A dermoscopy image of a single skin lesion; a male patient, approximately 45 years of age: 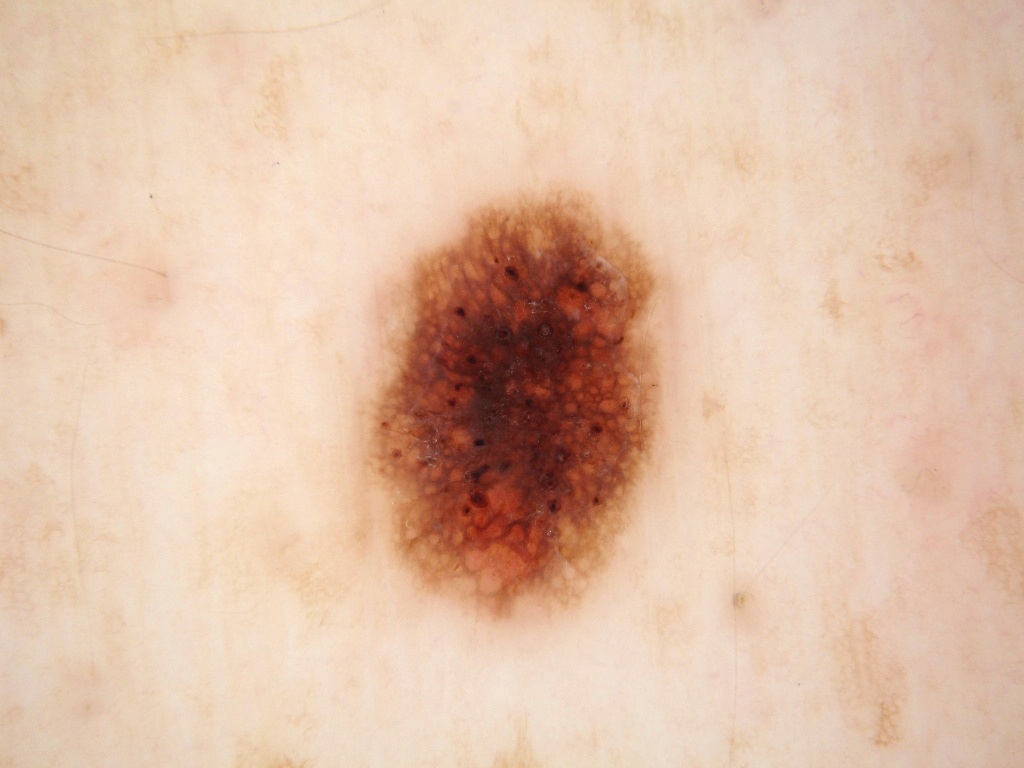Findings:
• bounding box · x1=355, y1=188, x2=674, y2=622
• extent · moderate
• features · globules and pigment network
• diagnostic label · a melanocytic nevus